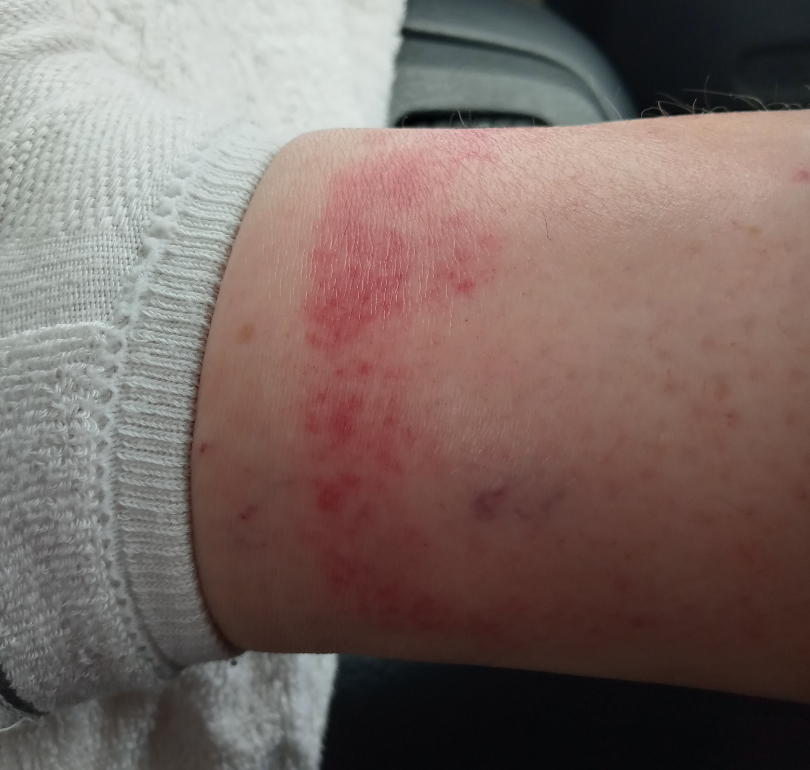This is a close-up image.
Symptoms reported: pain, enlargement, bothersome appearance, burning and darkening.
The patient also reports joint pain.
The lesion is described as raised or bumpy and flat.
The condition has been present for one to four weeks.
Self-categorized by the patient as a rash.
Located on the leg.
The differential includes Contact dermatitis and Allergic Contact Dermatitis, with no clear leading consideration.